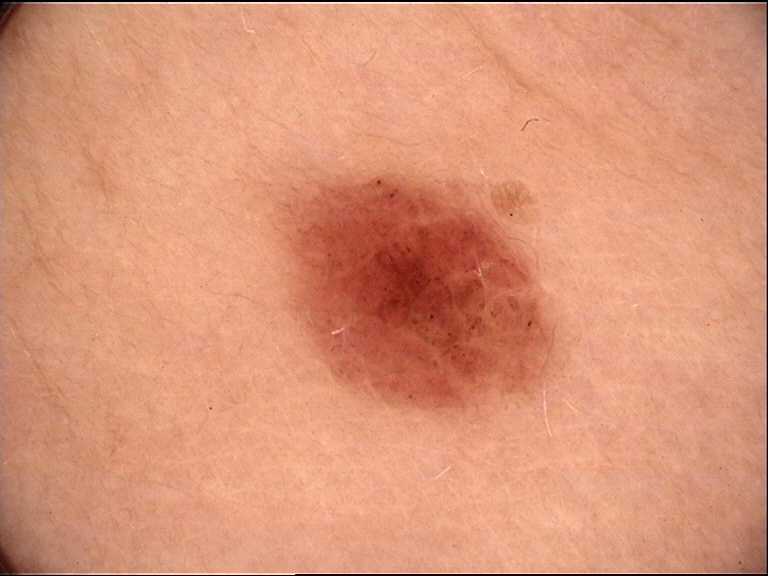<case>
  <diagnosis>
    <name>dysplastic compound nevus</name>
    <code>cd</code>
    <malignancy>benign</malignancy>
    <super_class>melanocytic</super_class>
    <confirmation>expert consensus</confirmation>
  </diagnosis>
</case>